Dermoscopy of a skin lesion, the subject is a male aged 83 or over — 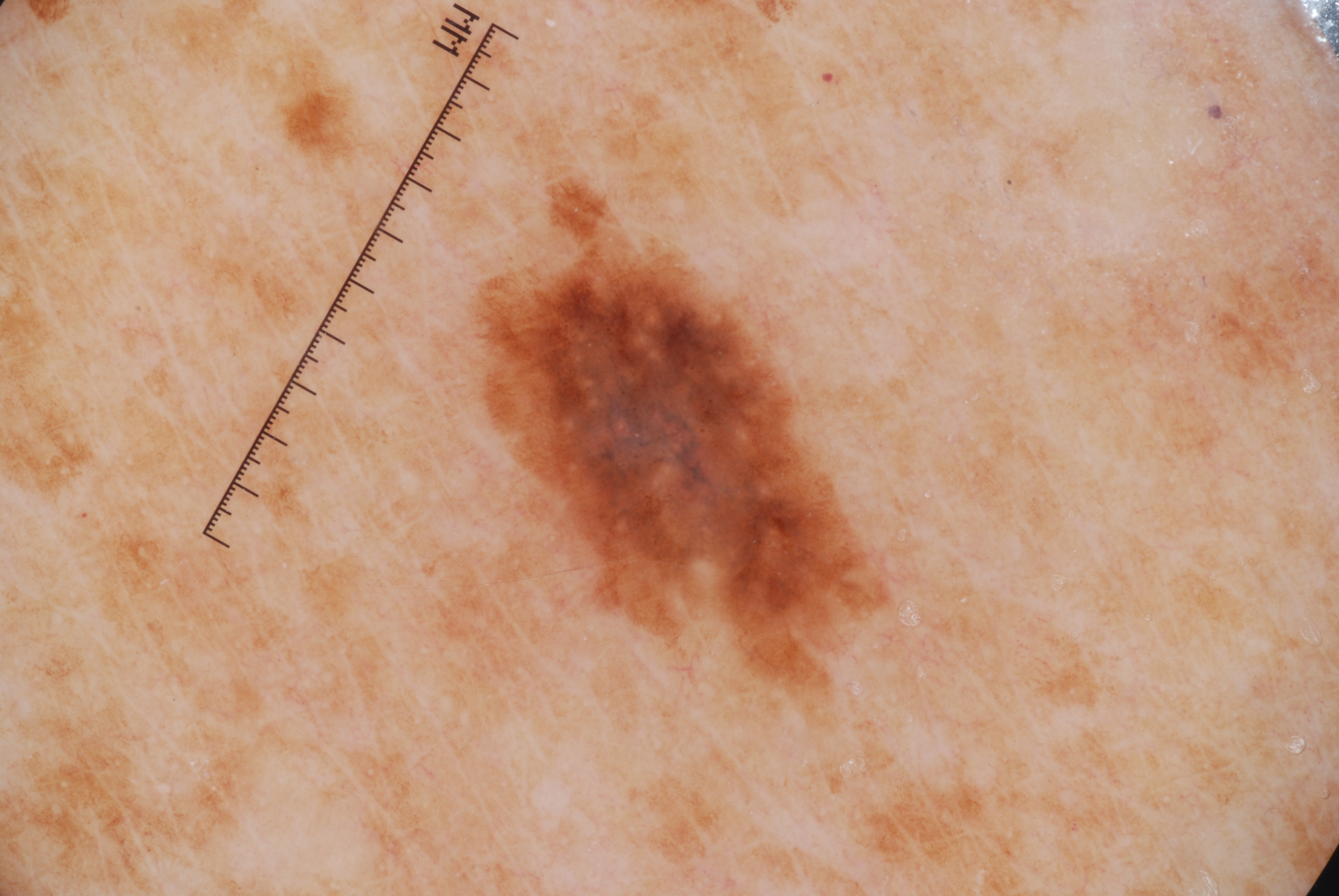lesion bbox — x1=481 y1=238 x2=878 y2=679; size — ~9% of the field; dermoscopic pattern — pigment network and milia-like cysts; assessment — a melanocytic nevus.